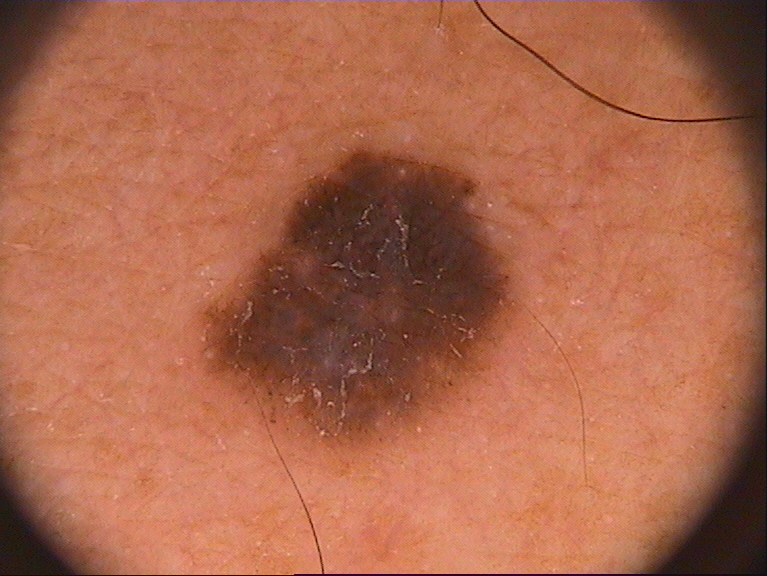A dermoscopic image of a skin lesion. Lesion location: x1=206, y1=142, x2=511, y2=435. Dermoscopic assessment notes globules. A mid-sized lesion within the field. Histopathology confirmed a melanoma.